A dermoscopy image of a single skin lesion:
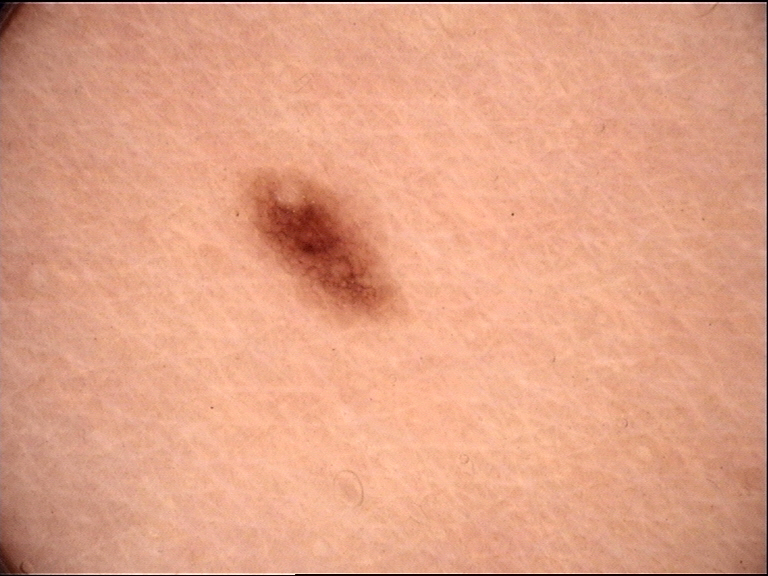Classified as a benign lesion — a dysplastic junctional nevus.